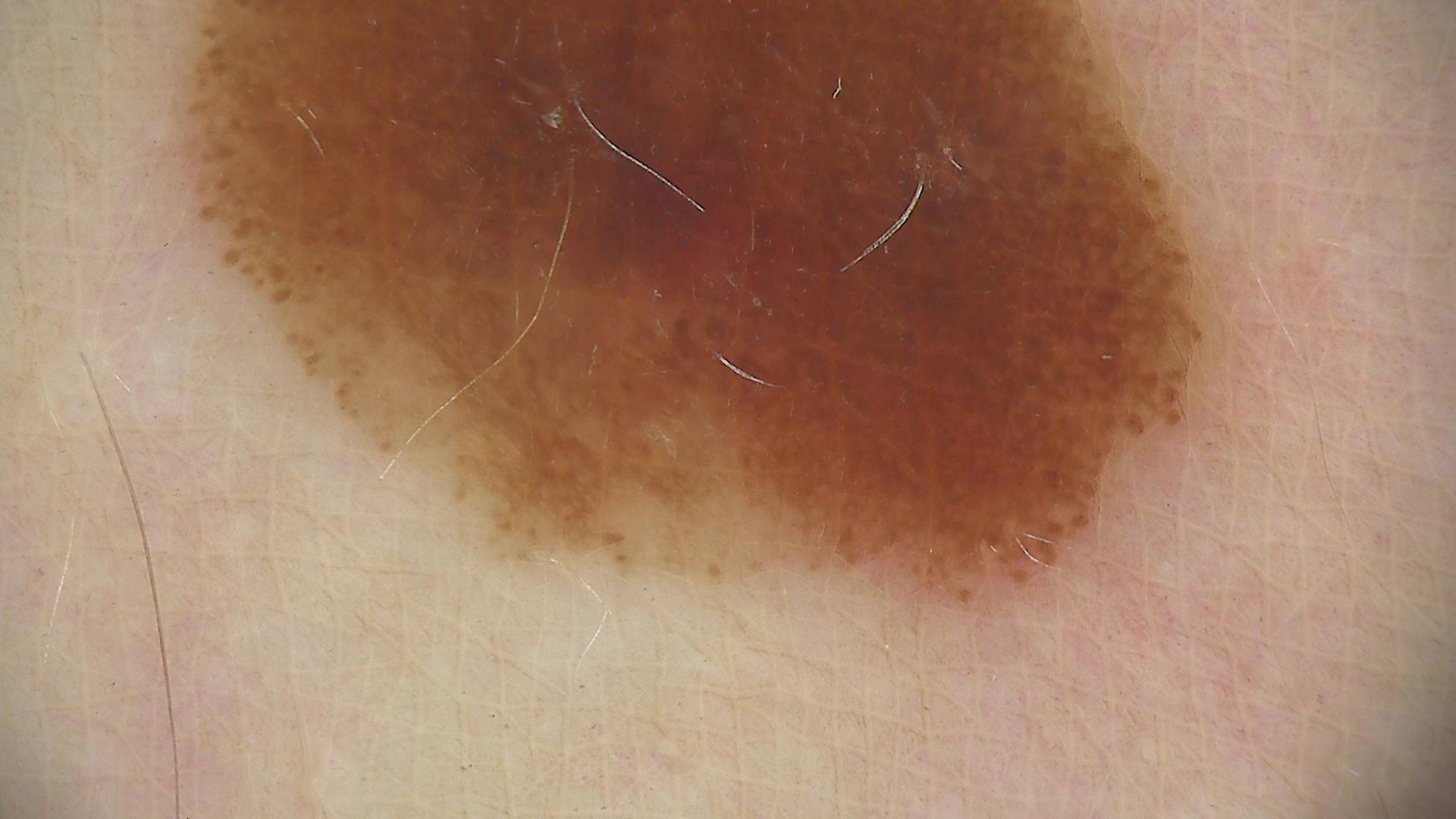Labeled as a dysplastic junctional nevus.